This image was taken at an angle. The contributor reports the condition has been present for about one day. The lesion involves the front of the torso:
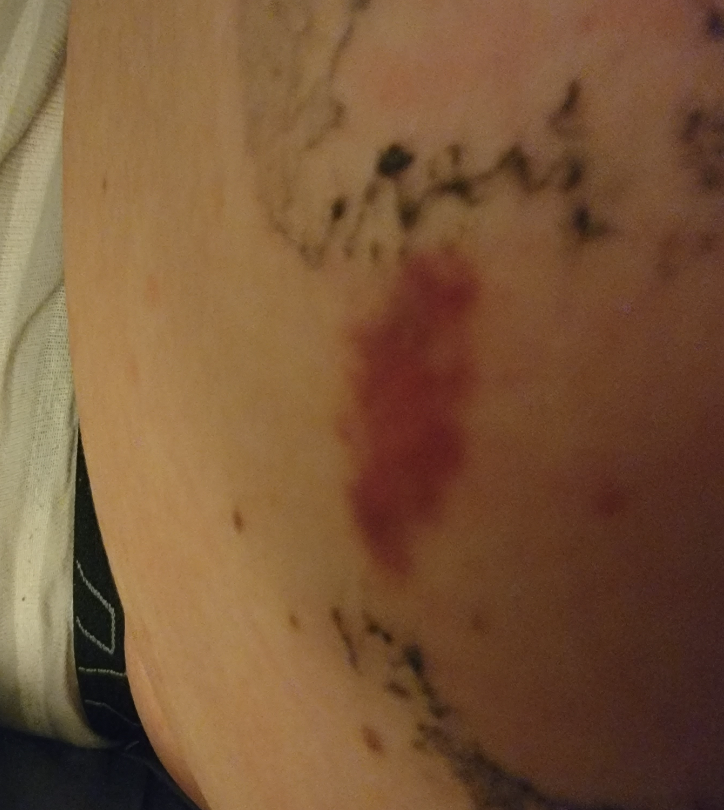Findings:
- assessment: unable to determine